Present for less than one week · the lesion is described as raised or bumpy · an image taken at an angle · no relevant systemic symptoms · the patient described the issue as a rash · the affected area is the leg and arm · the lesion is associated with burning and itching · female subject, age 40–49:
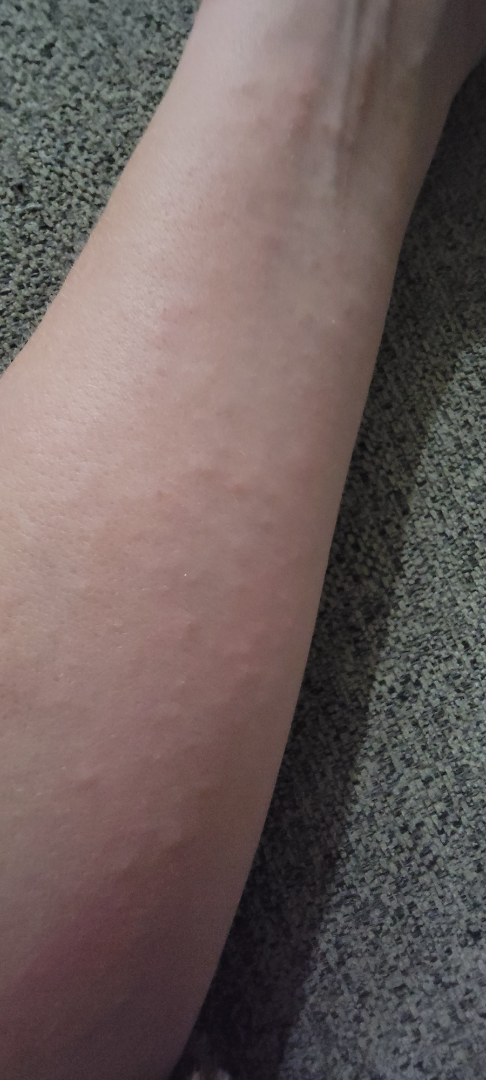On remote review of the image: Allergic Contact Dermatitis (0.55); Lichenoid myxedema (0.27); Viral Exanthem (0.18).